A clinical photograph of a skin lesion · Fitzpatrick II.
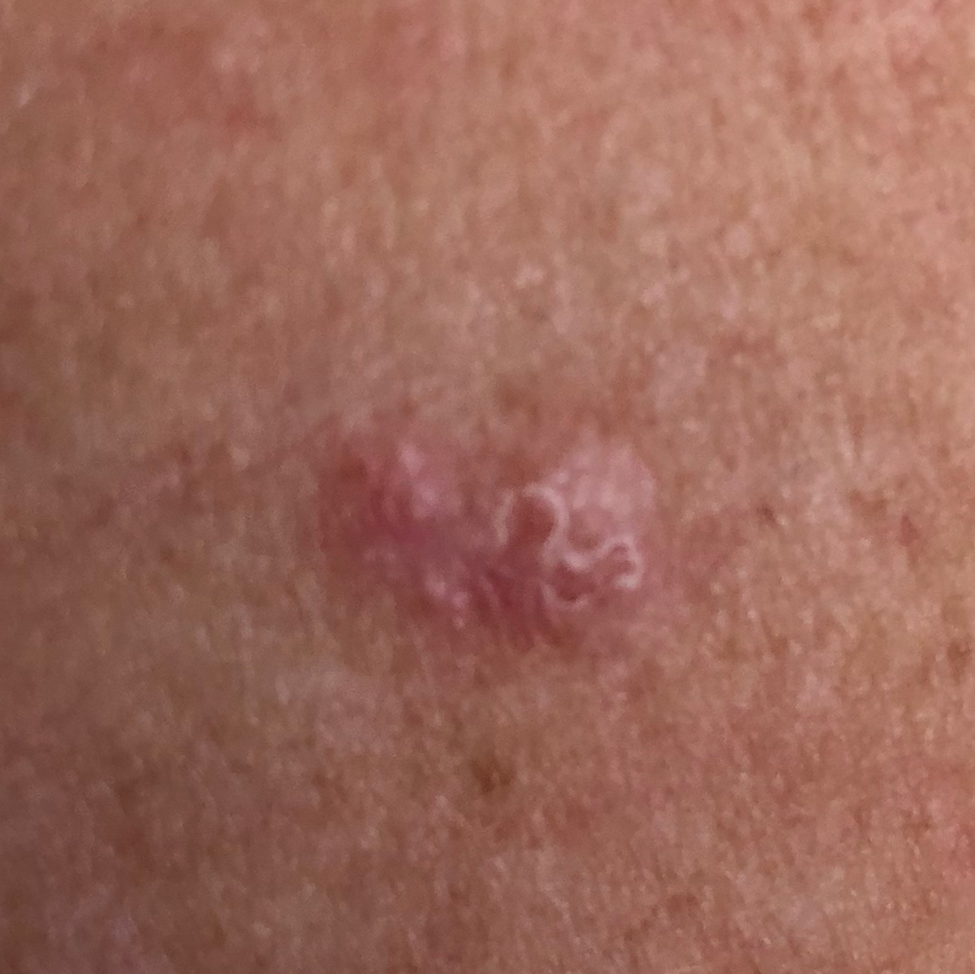site = the chest
lesion size = 14x9 mm
symptoms = itching, elevation / no pain
pathology = basal cell carcinoma (biopsy-proven)